A dermoscopic close-up of a skin lesion: 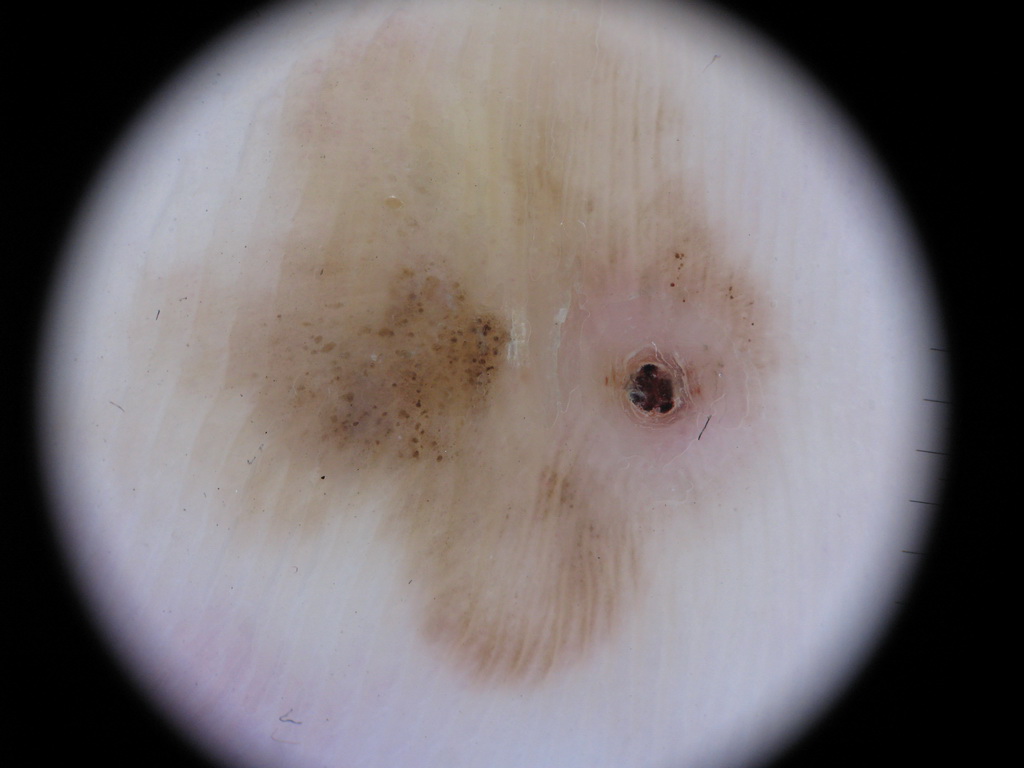{"lesion_location": {"bbox_xyxy": [100, 1, 805, 694]}, "diagnosis": {"name": "melanoma", "malignancy": "malignant", "lineage": "melanocytic", "provenance": "histopathology"}}